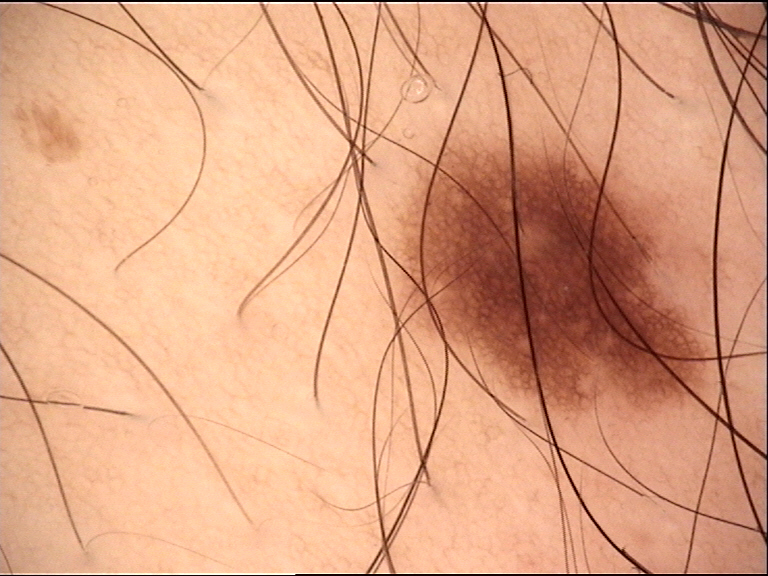A skin lesion imaged with a dermatoscope. Classified as a banal lesion — a junctional nevus.